A clinical photograph of a skin lesion: 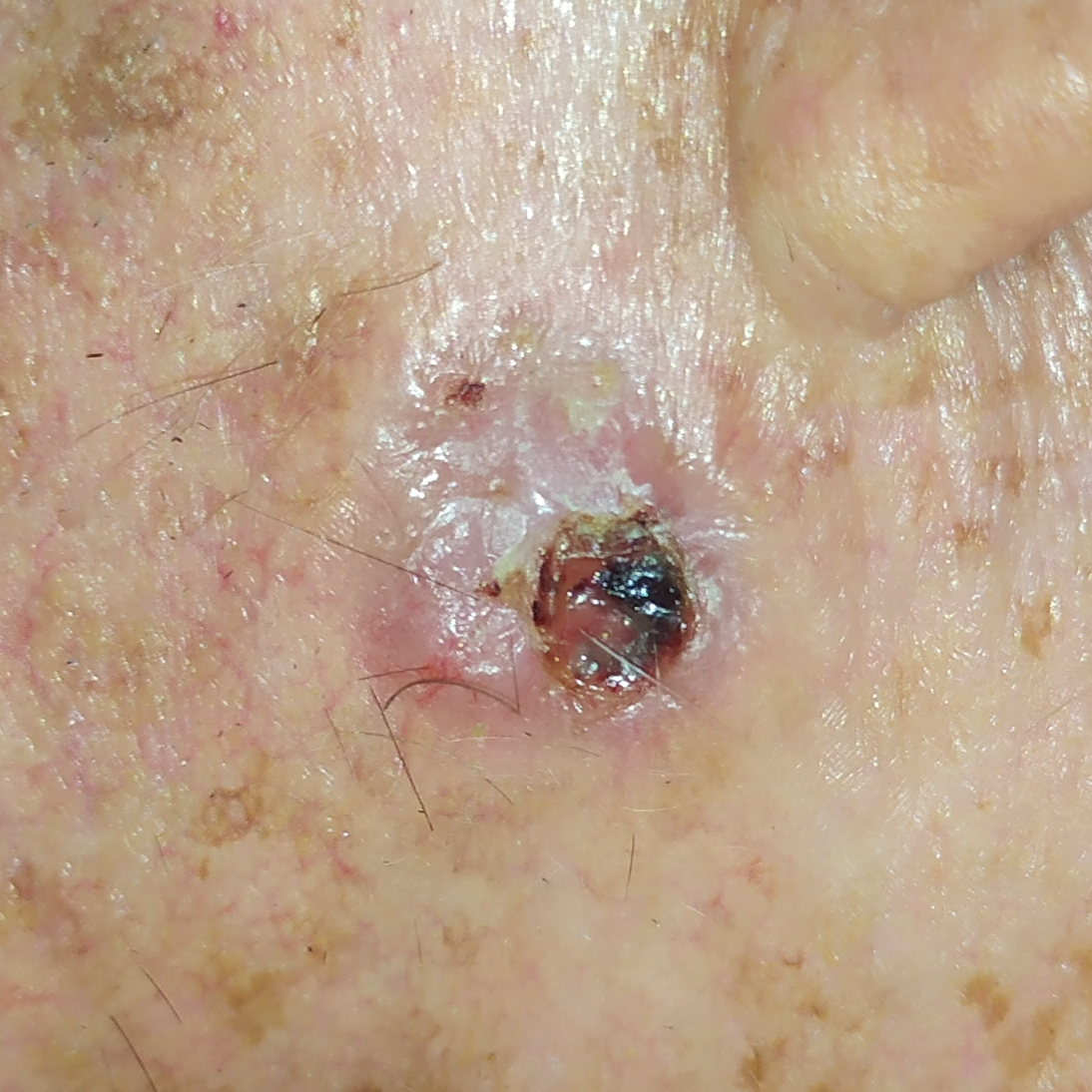Summary:
The lesion is on the face. The patient describes that the lesion has changed, itches, has grown, is elevated, and has bled, but does not hurt.
Conclusion:
Histopathologically confirmed as a basal cell carcinoma.